A dermoscopic photograph of a skin lesion.
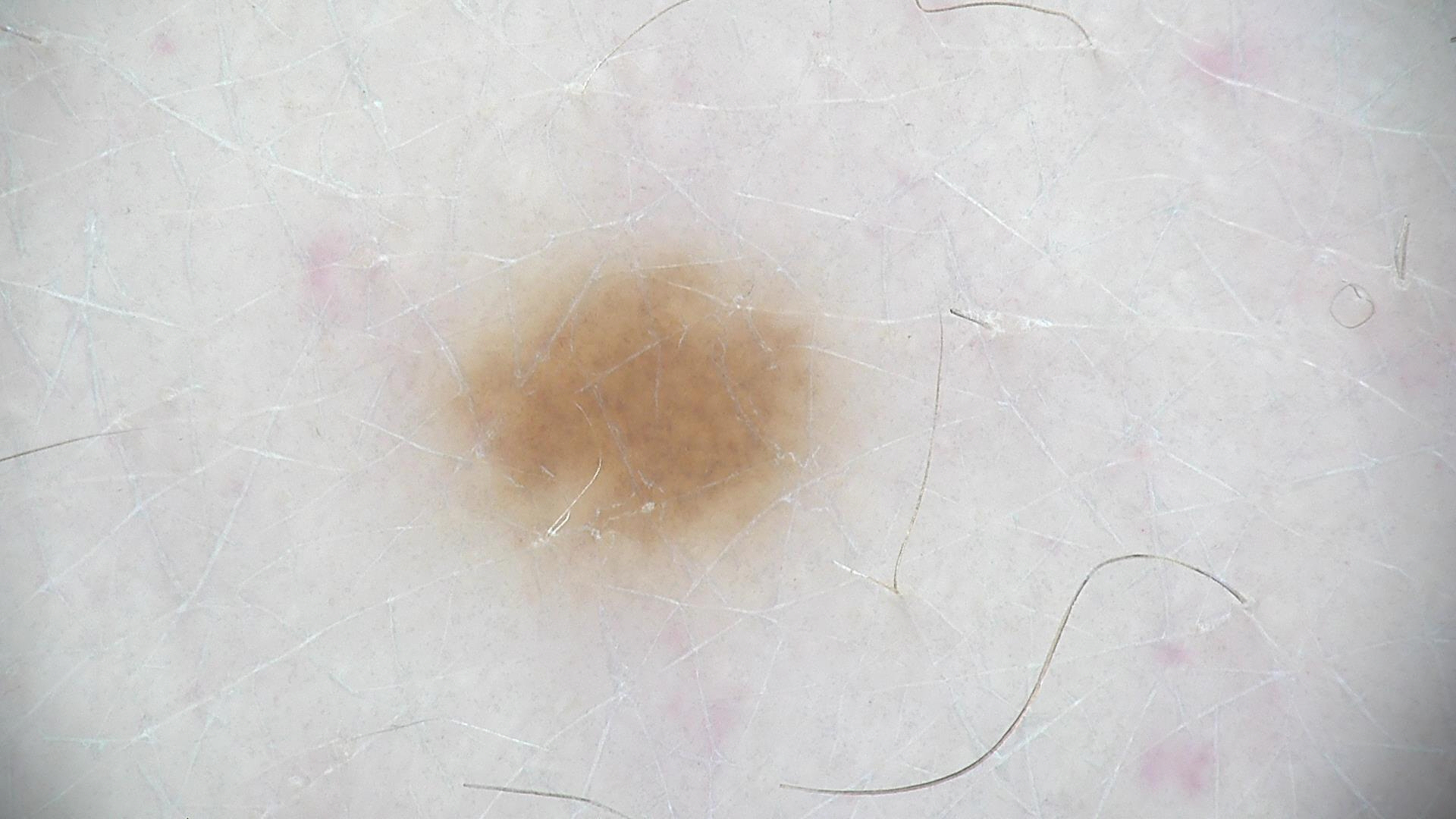Diagnosed as a benign lesion — a dysplastic junctional nevus.